A male patient aged 62 · a clinical photograph showing a skin lesion · the patient was assessed as Fitzpatrick phototype III:
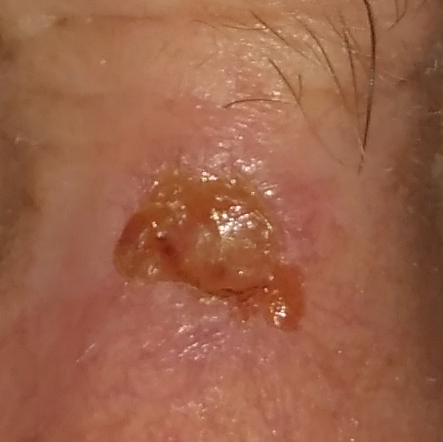The lesion is roughly 7 by 5 mm. Confirmed on histopathology as a basal cell carcinoma.